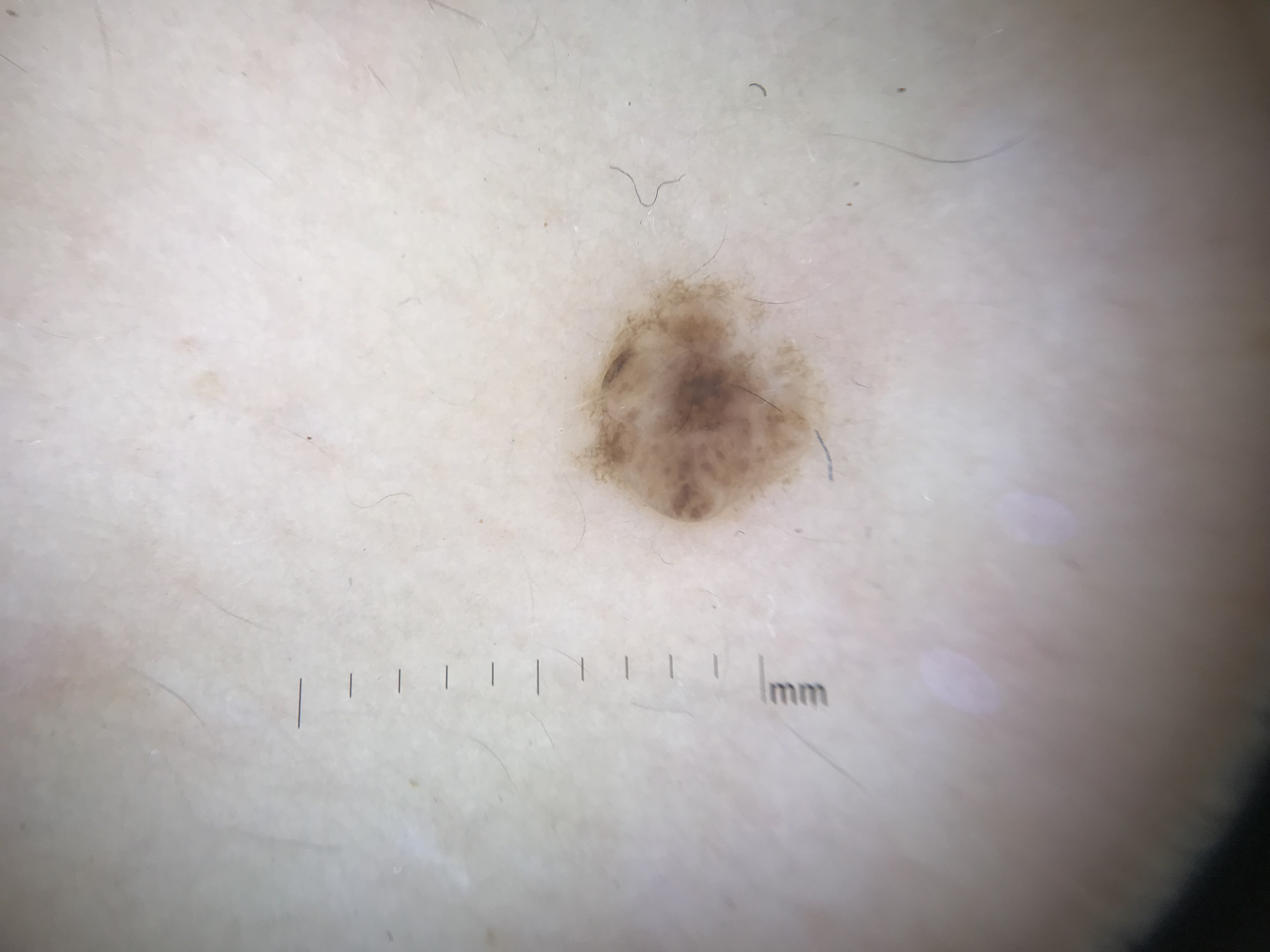A skin lesion imaged with a dermatoscope.
This is a banal lesion.
The diagnostic label was a dermal nevus.